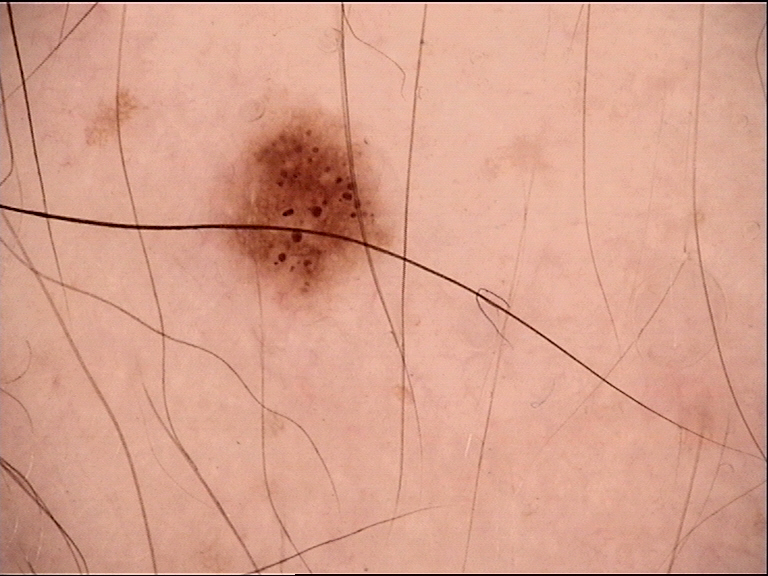Labeled as a dysplastic junctional nevus.